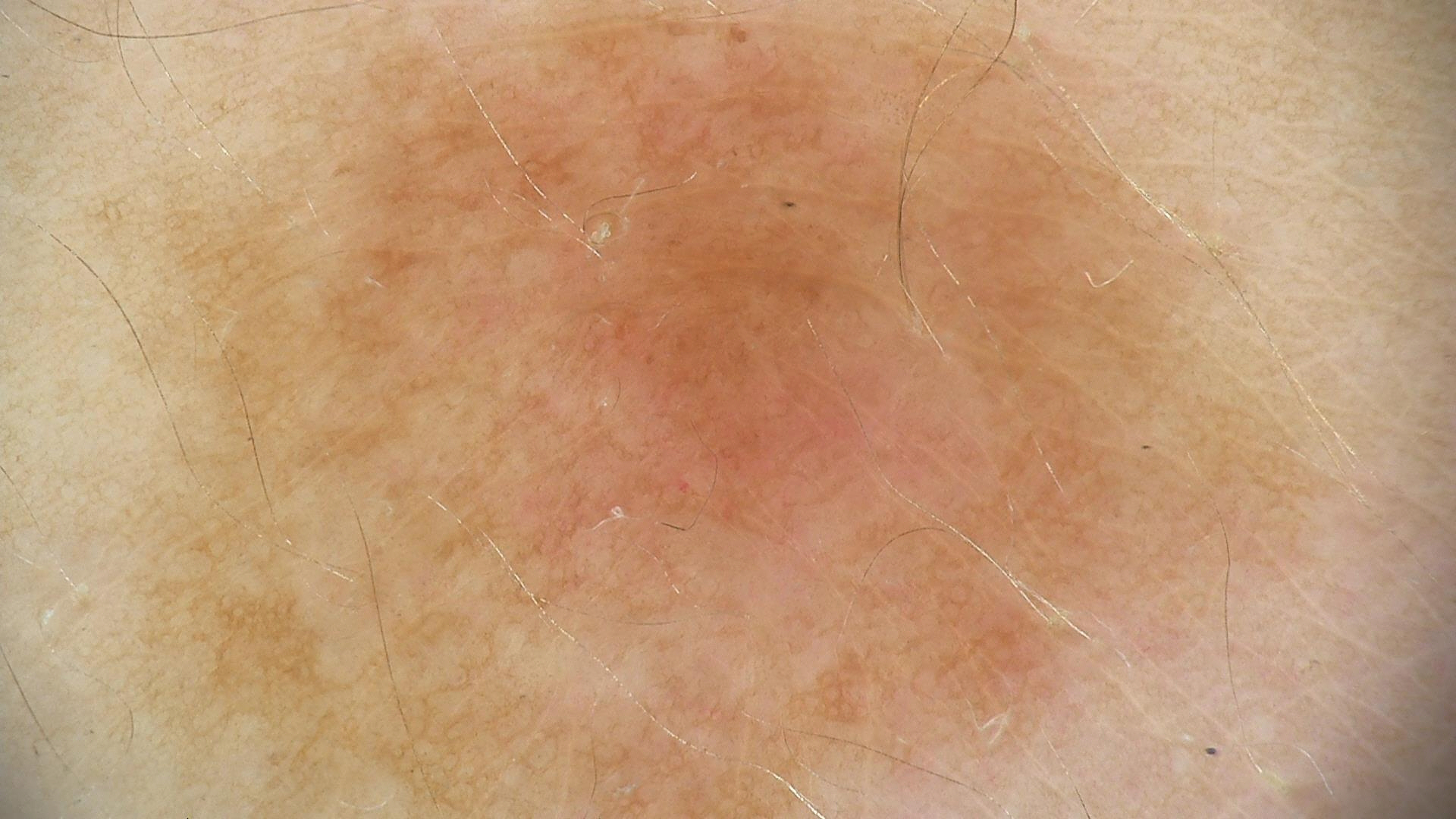A dermoscopic photograph of a skin lesion.
This is a banal lesion.
The diagnosis was a compound nevus.